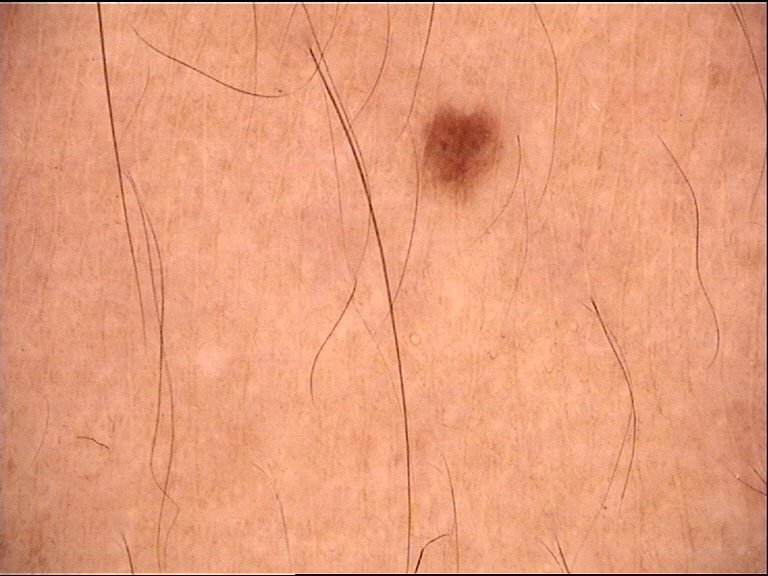A dermoscopic image of a skin lesion.
Labeled as a dysplastic junctional nevus.